A female subject approximately 65 years of age — 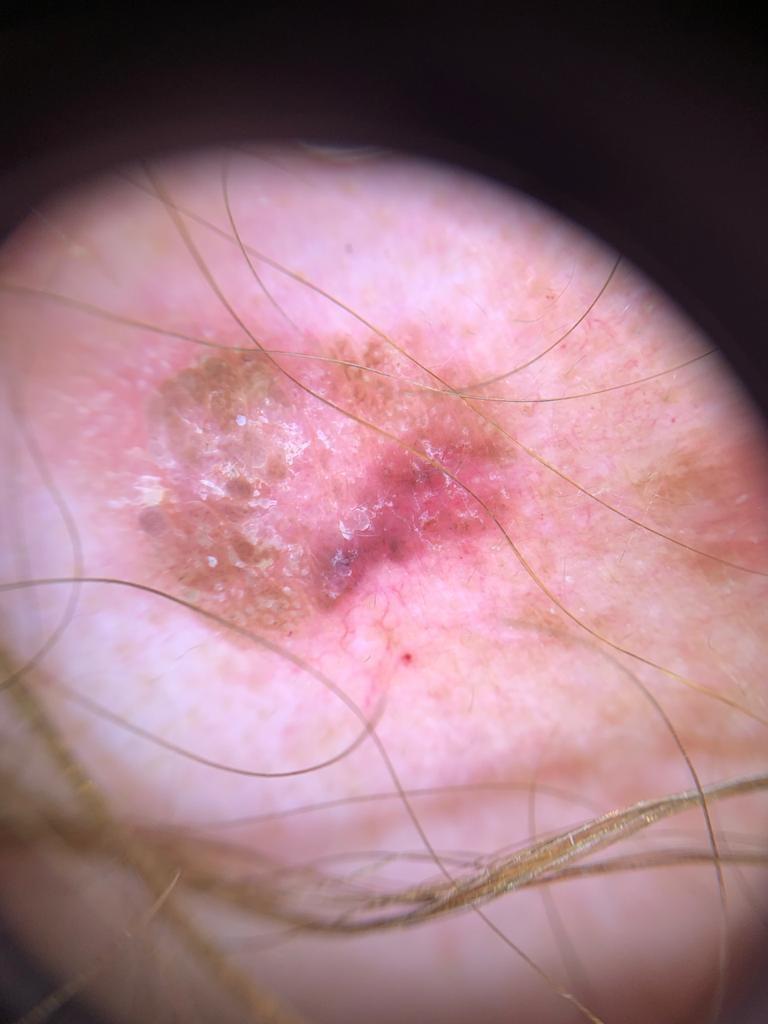The lesion was found on the head or neck.
Confirmed on histopathology as a basal cell carcinoma.